Female patient, age 60–69. Present for one to four weeks. A close-up photograph. The contributor notes pain, bothersome appearance, itching and burning. The contributor notes the lesion is flat. Located on the leg. No constitutional symptoms were reported — 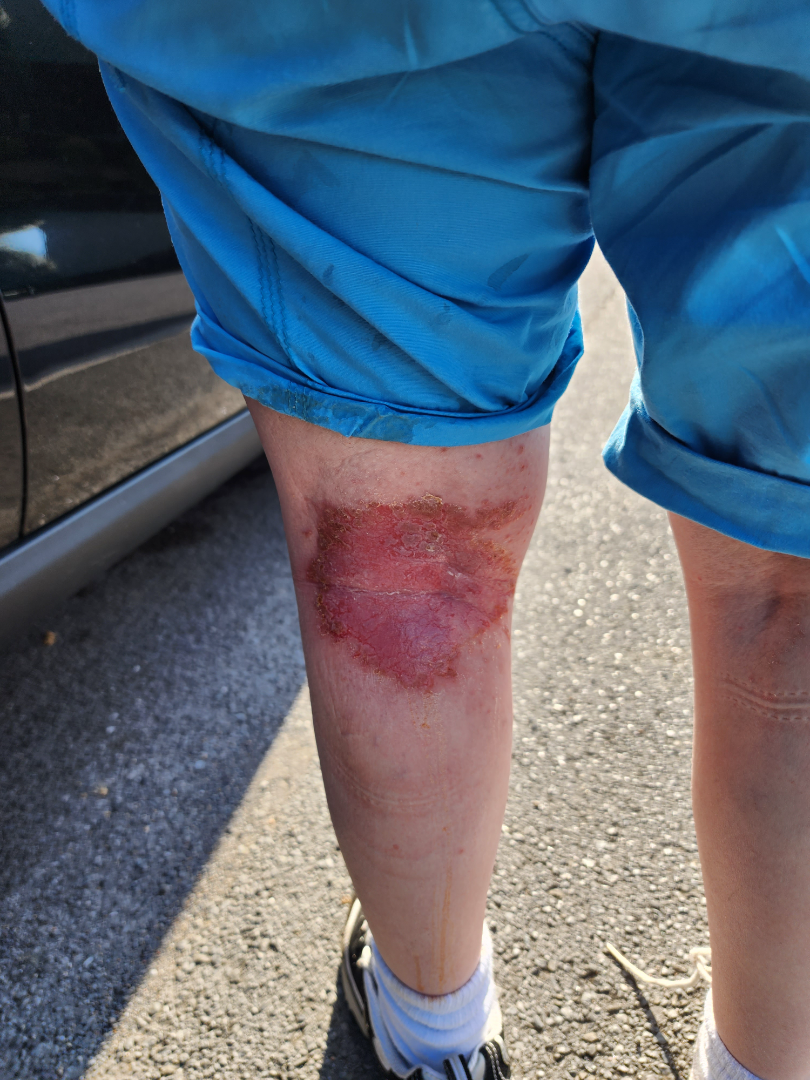Review: The primary impression is Infected eczema; also raised was Psoriasis; also consider Localized skin infection.